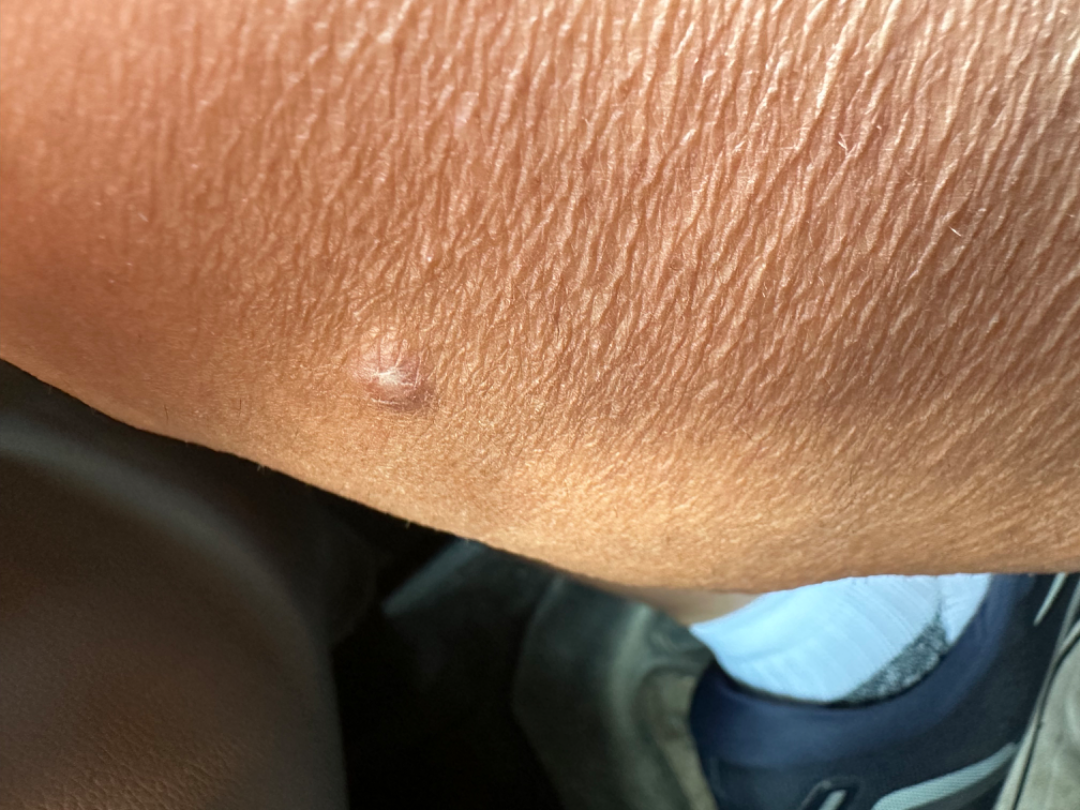{
  "assessment": "ungradable on photographic review"
}